The patient was assessed as FST II · a female subject about 80 years old · a contact-polarized dermoscopy image of a skin lesion:
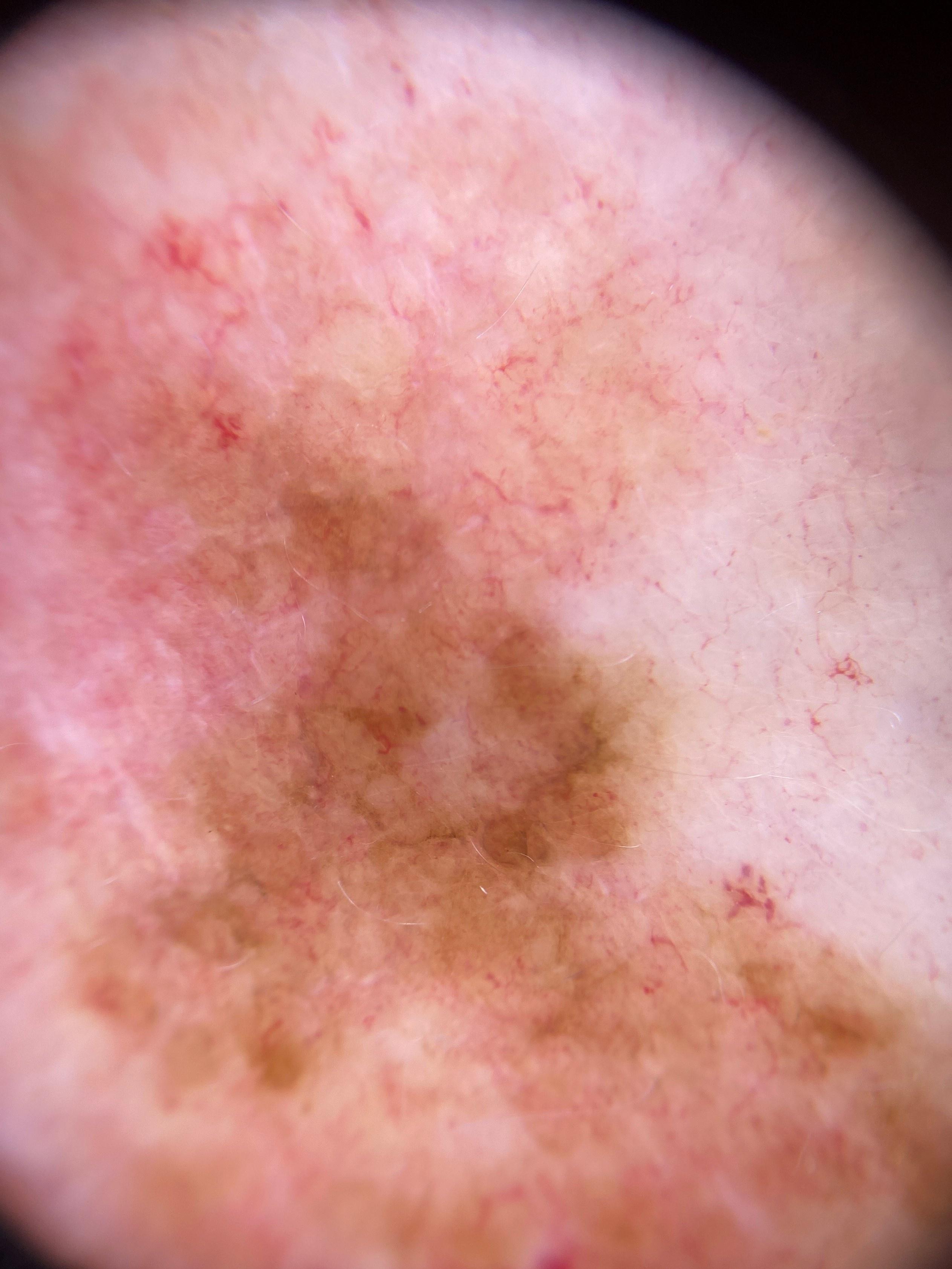Case summary:
The lesion involves an upper extremity.
Pathology:
Biopsy-confirmed as a melanoma.